The front of the torso is involved, the subject is a female aged 50–59, the photograph was taken at an angle.
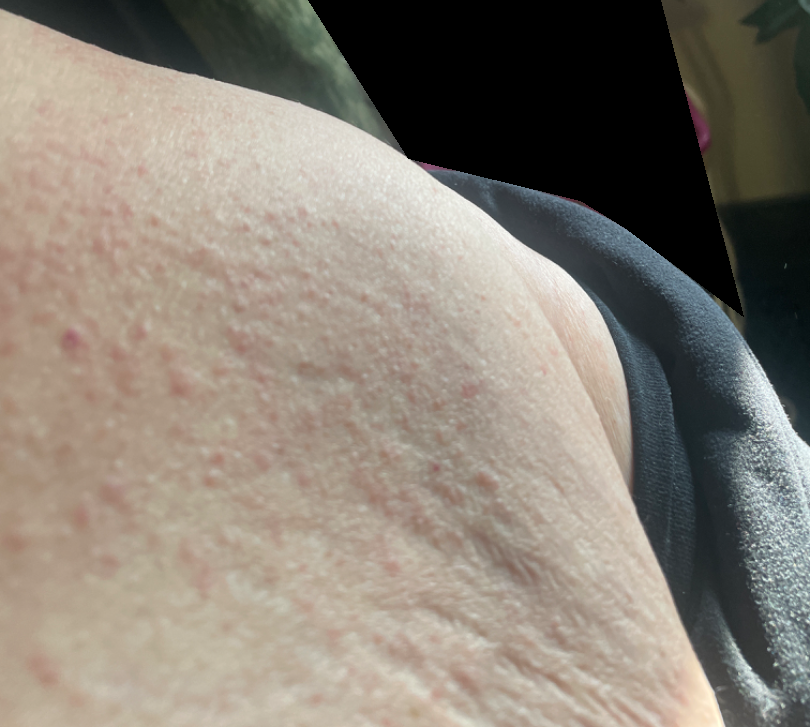systemic_symptoms:
  - chills
  - fatigue
texture: raised or bumpy
skin_tone:
  fitzpatrick: II
  monk_skin_tone: 2
symptoms:
  - itching
  - burning
duration: less than one week
patient_category: a rash
differential:
  leading:
    - Allergic Contact Dermatitis
  considered:
    - Hypersensitivity
  unlikely:
    - Drug Rash
    - Eczema